A skin lesion imaged with a dermatoscope.
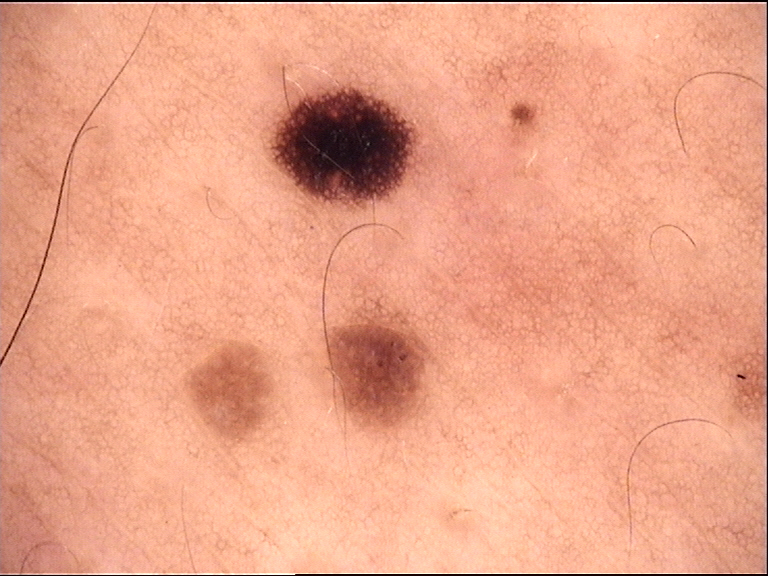{"lesion_type": {"main_class": "banal", "pattern": "junctional"}, "diagnosis": {"name": "junctional nevus", "code": "jb", "malignancy": "benign", "super_class": "melanocytic", "confirmation": "expert consensus"}}